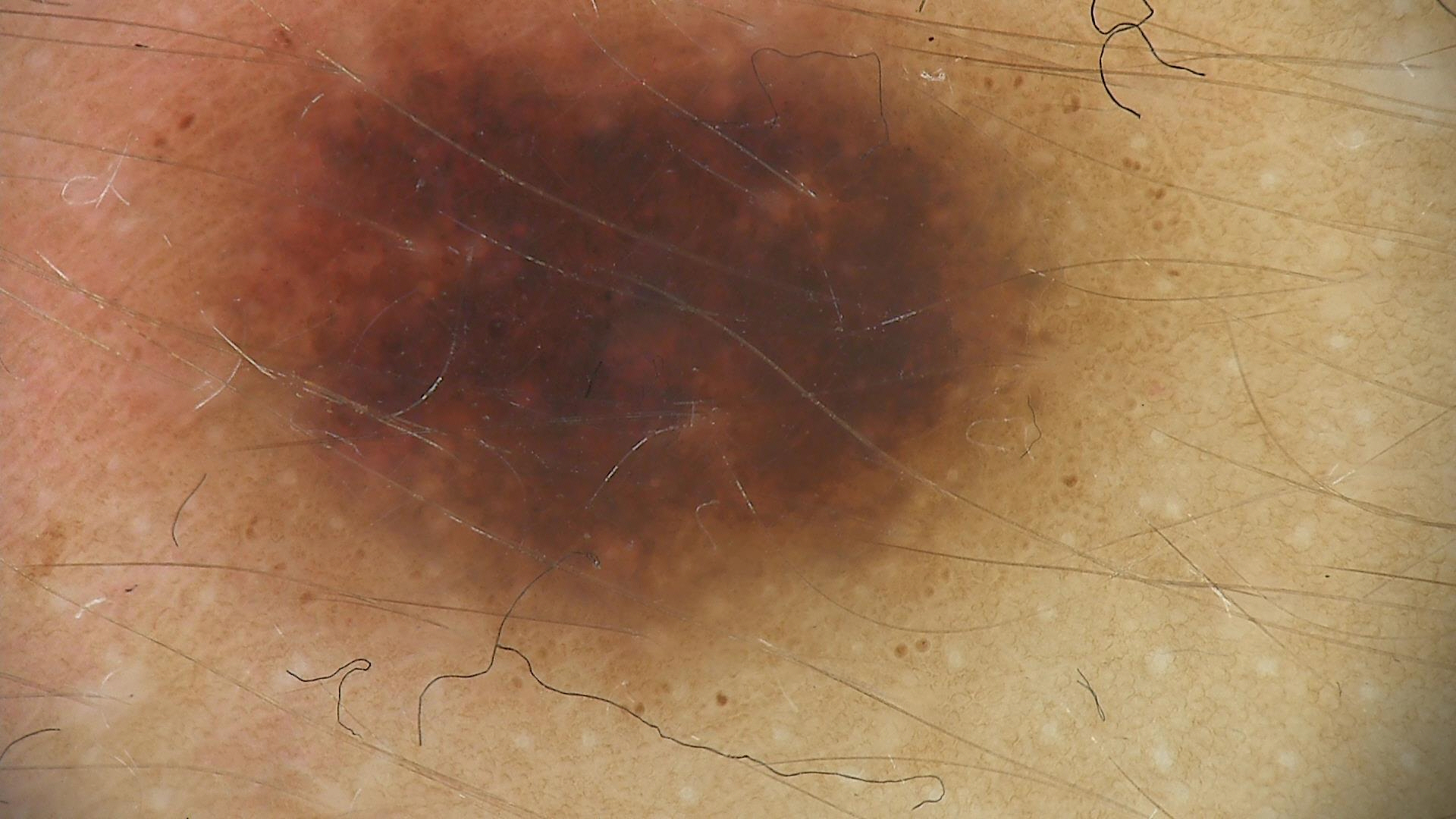The diagnosis was a dysplastic compound nevus.